Located on the arm · self-categorized by the patient as a rash · the subject is male · the contributor notes bothersome appearance, burning and itching · this image was taken at an angle · reported duration is less than one week · texture is reported as raised or bumpy.
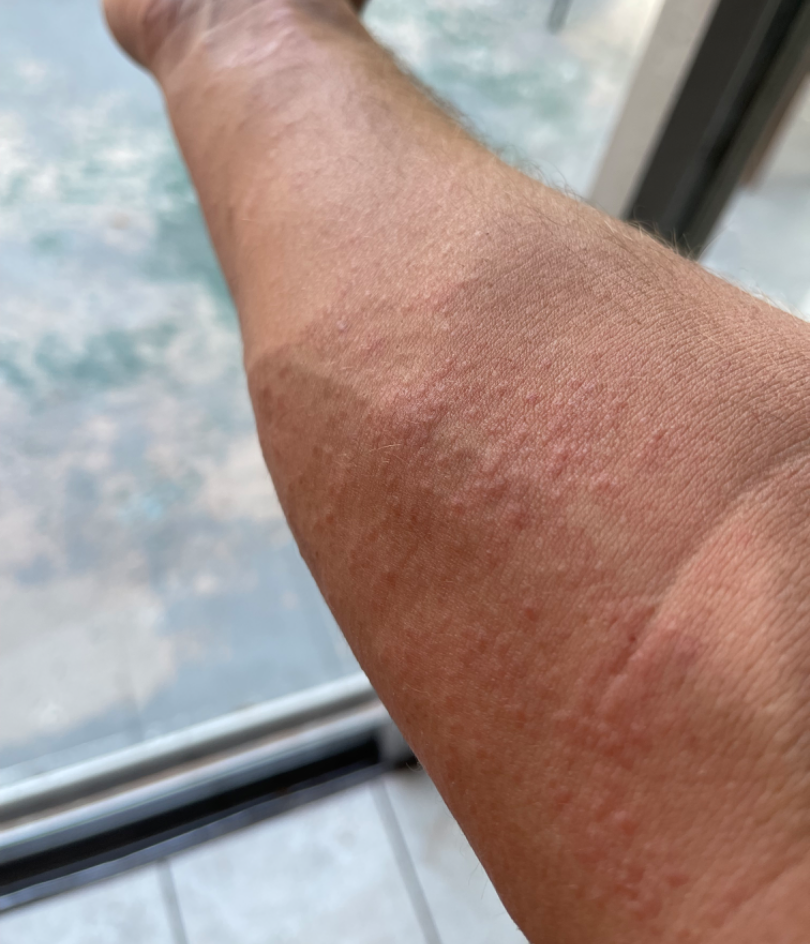differential: Acute dermatitis, NOS (considered); Eczema (considered); Contact dermatitis (considered); Allergic Contact Dermatitis (lower probability).